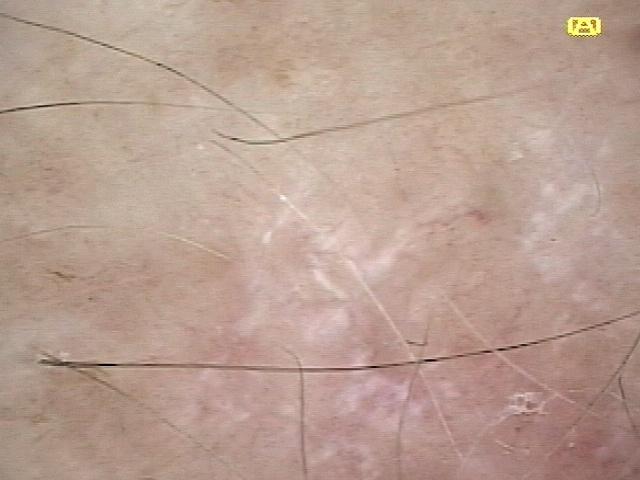Diagnosis: Histopathologically confirmed as a squamous cell carcinoma.